A dermoscopic image of a skin lesion — 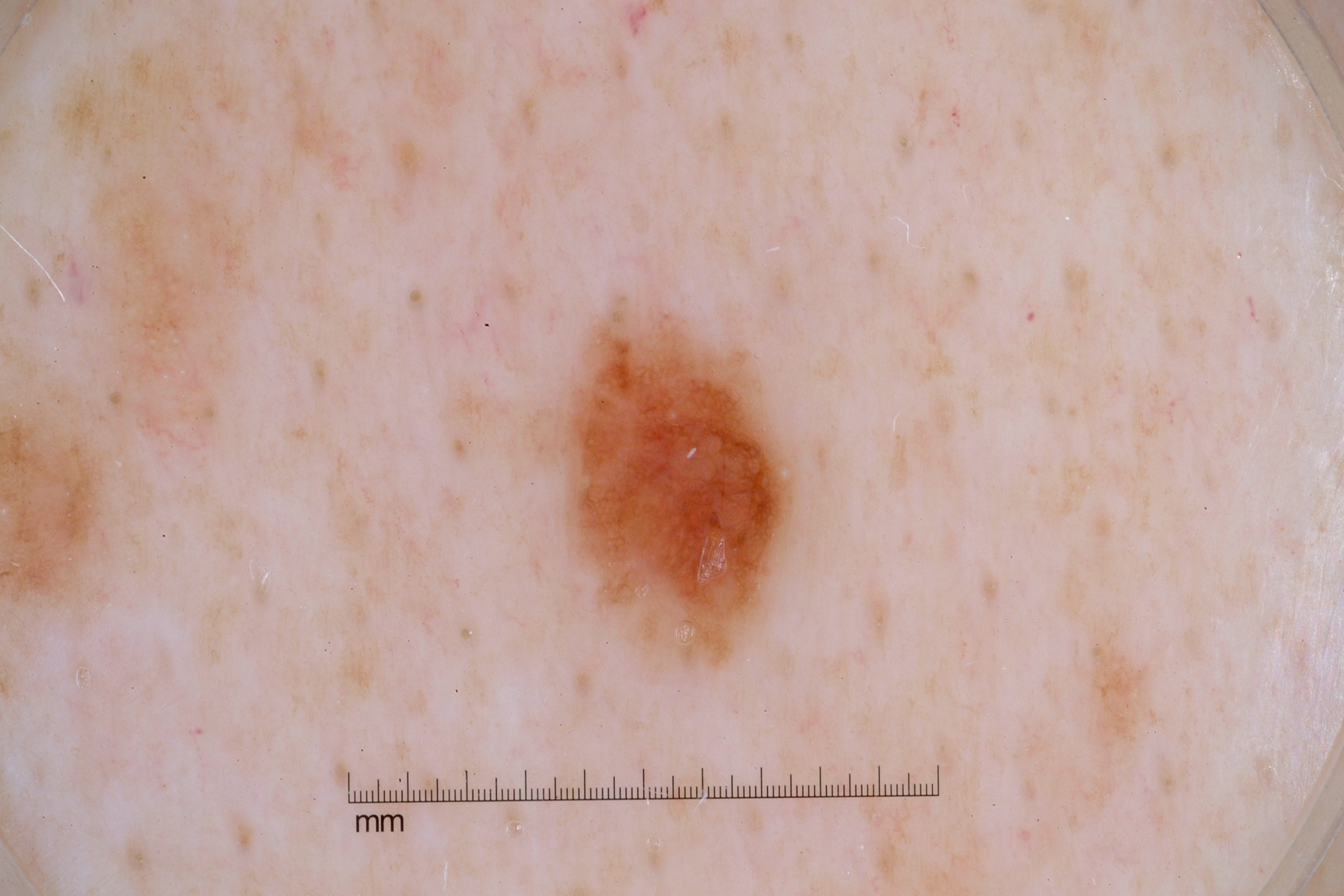With coordinates (x1, y1, x2, y2), lesion location: 546, 315, 797, 658. The clinical diagnosis was a melanocytic nevus, a benign skin lesion.